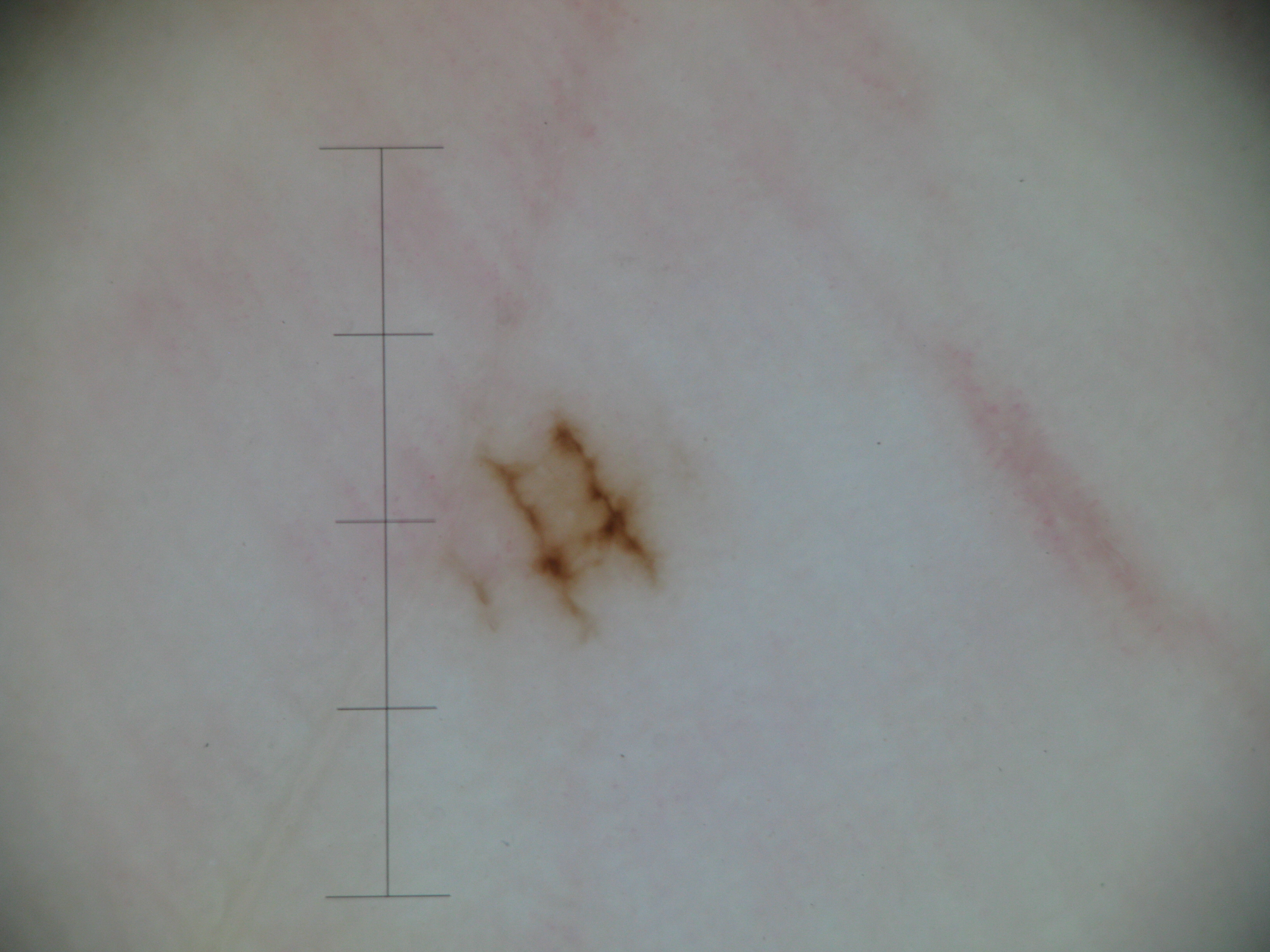Summary:
A dermoscopy image of a single skin lesion.
Conclusion:
Classified as a banal lesion — an acral junctional nevus.